A dermoscopic close-up of a skin lesion.
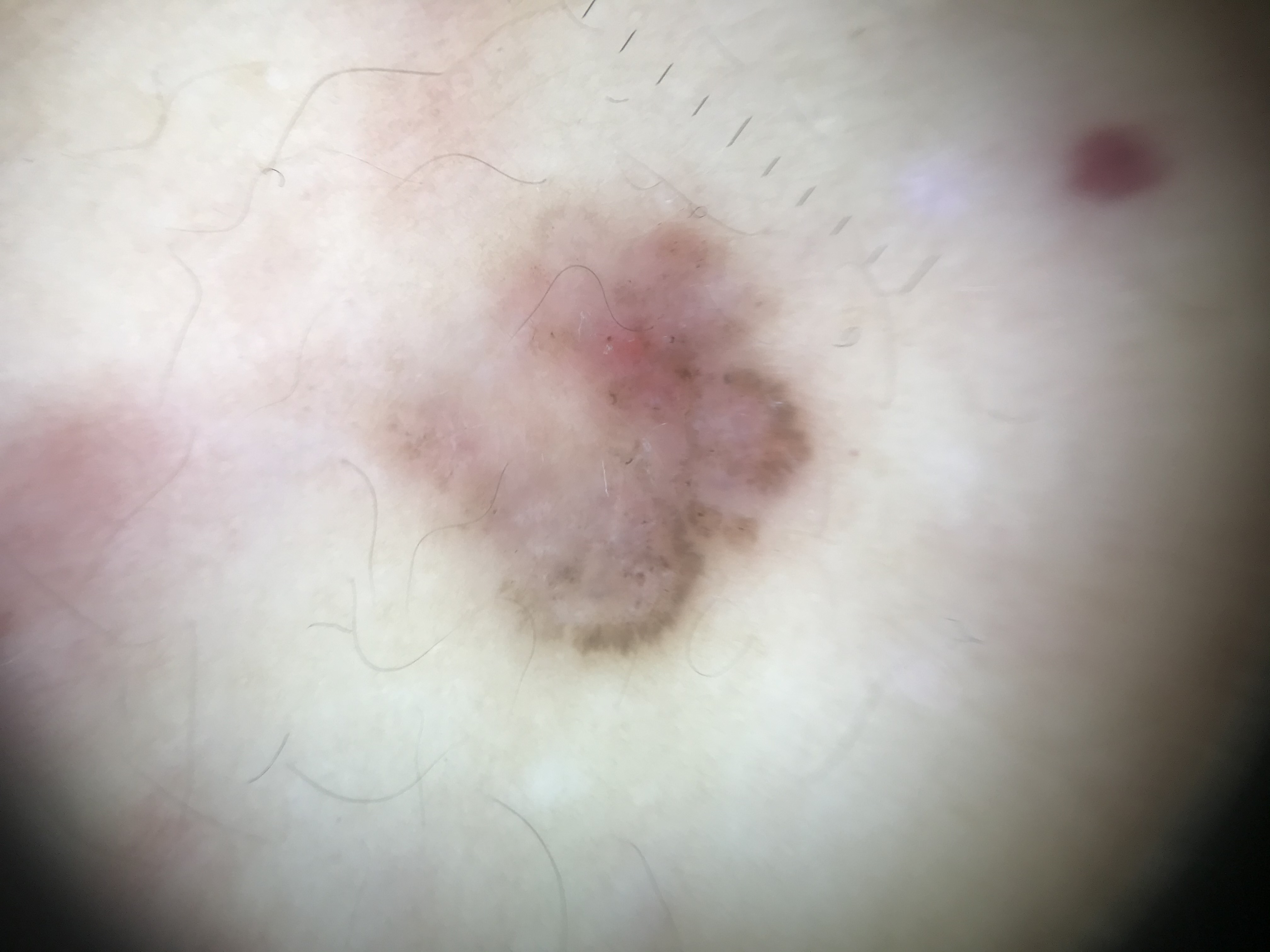This is a keratinocytic lesion. Histopathology confirmed a skin cancer — a basal cell carcinoma.